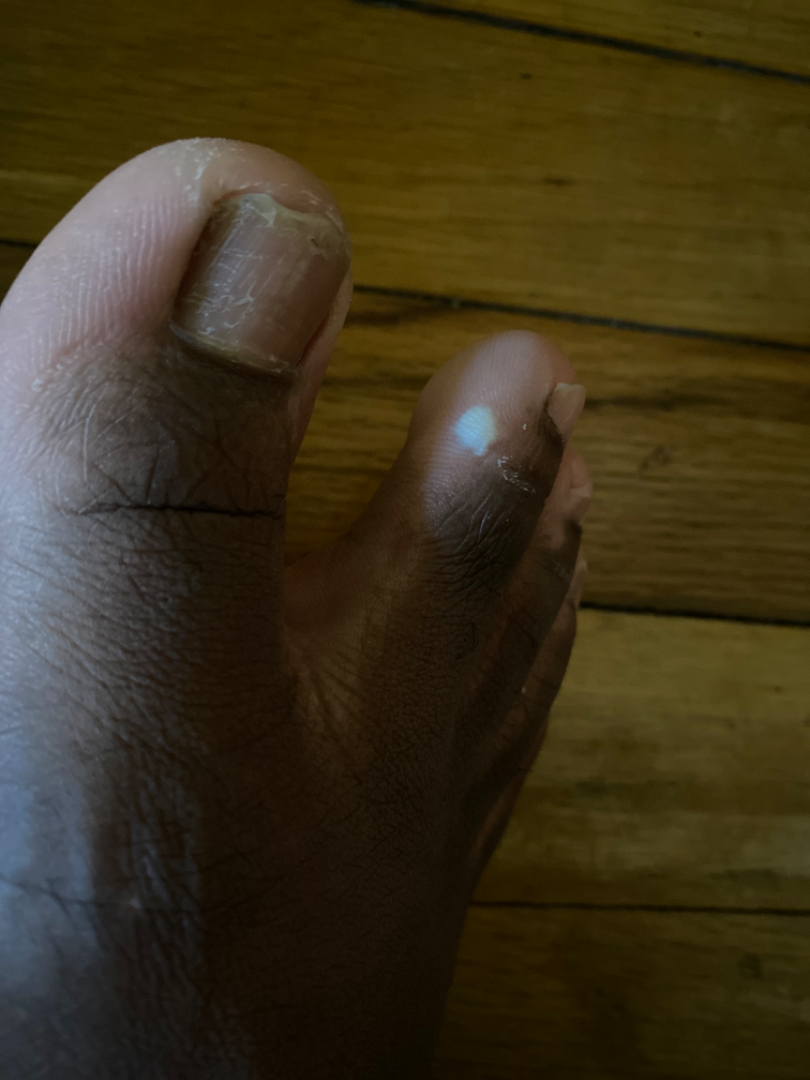Q: Reported symptoms?
A: bothersome appearance
Q: Duration?
A: about one day
Q: What is the framing?
A: close-up
Q: What is the affected area?
A: top or side of the foot
Q: Who is the patient?
A: male, age 18–29
Q: How does the lesion feel?
A: fluid-filled